A dermoscopy image of a single skin lesion.
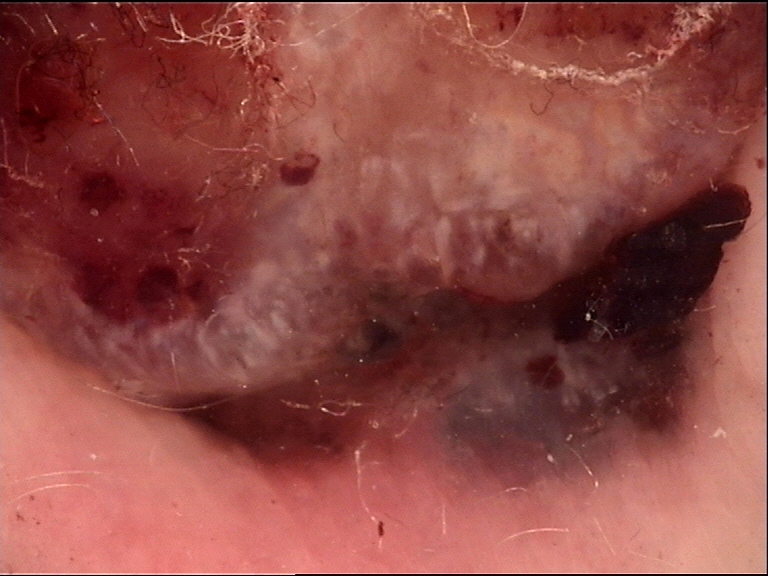Histopathology confirmed a malignant lesion — a melanoma.